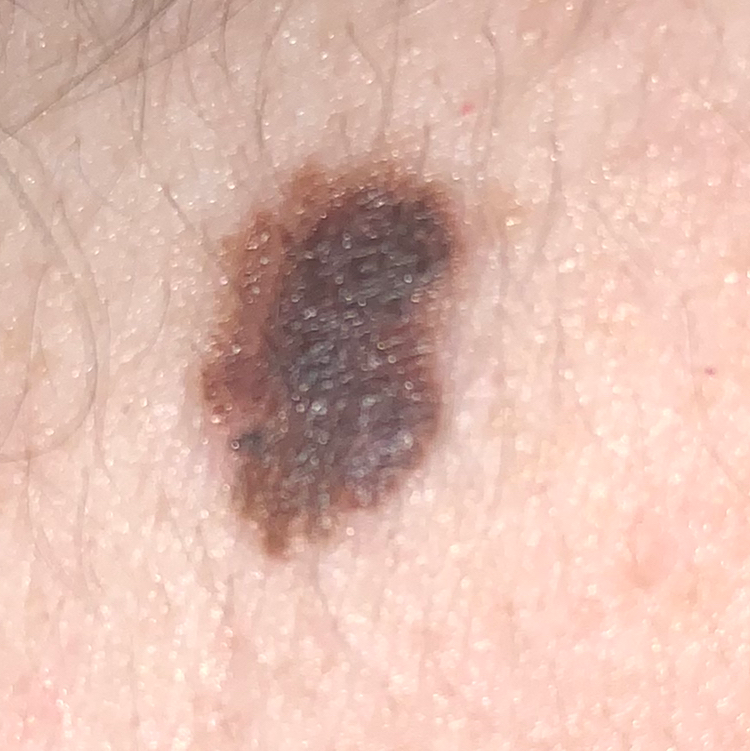History notes prior malignancy (patient or family).
Fitzpatrick IV.
A female subject 43 years of age.
A clinical photo of a skin lesion taken with a smartphone.
Located on the neck.
The lesion measures 20 × 8 mm.
The patient reports that the lesion has grown, but has not bled.
Histopathology confirmed a melanoma.